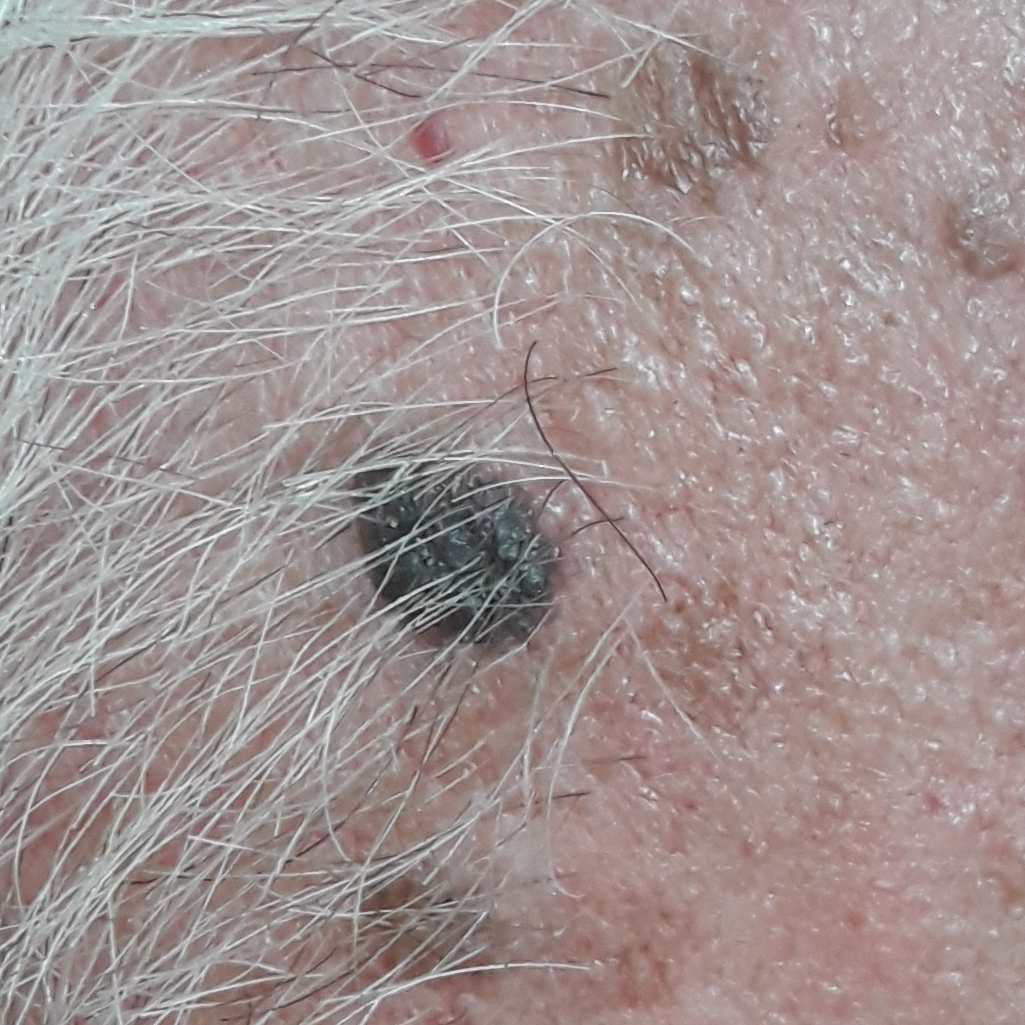Findings:
– risk factors — prior skin cancer (patient or family), alcohol use, no tobacco use
– subject — male, 69 years of age
– FST — II
– body site — the face
– lesion diameter — 10 × 5 mm
– impression — seborrheic keratosis (clinical consensus)